Located on the arm. This is a close-up image. The subject is 40–49, female: 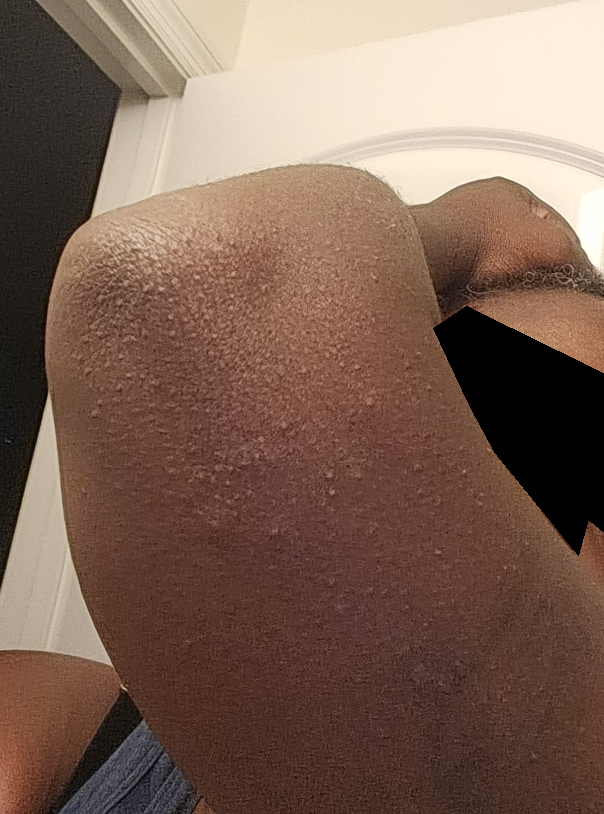  skin_tone:
    fitzpatrick: VI
  patient_category: a rash
  duration: one to four weeks
  systemic_symptoms: none reported
  differential:
    leading:
      - Keratosis pilaris